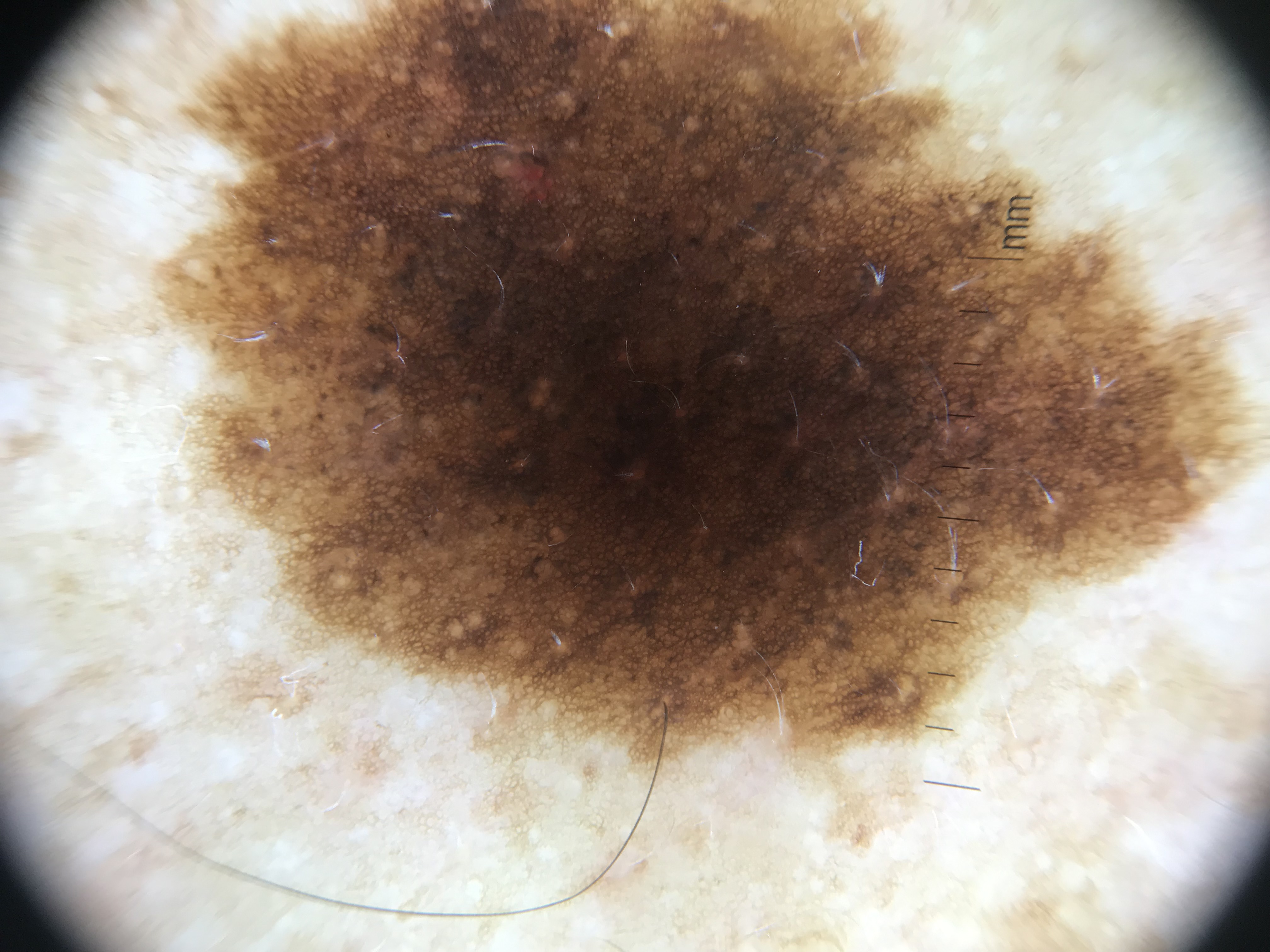Findings:
A dermatoscopic image of a skin lesion.
Conclusion:
Labeled as a benign lesion — a dysplastic compound nevus.